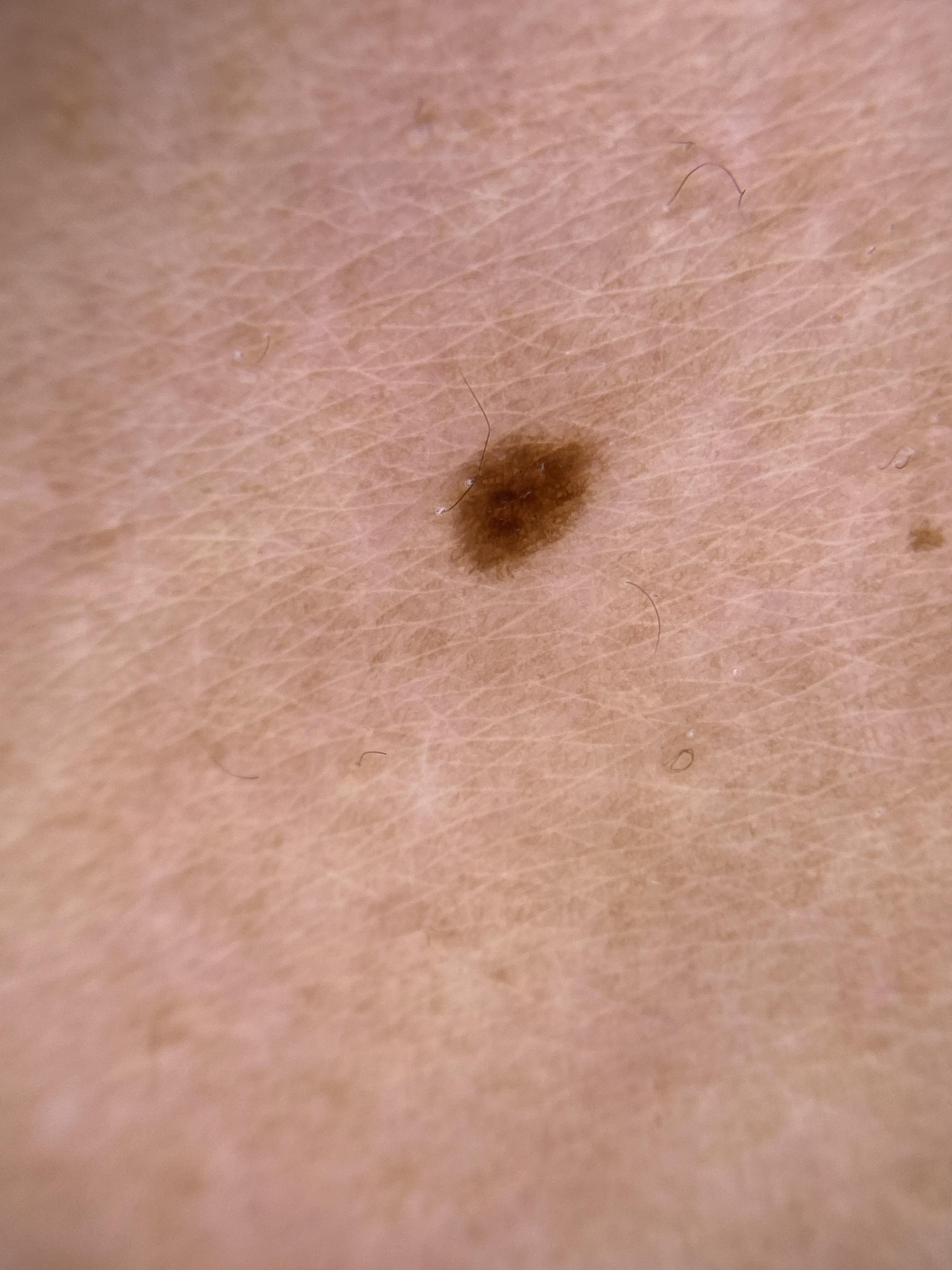A dermoscopic photograph of a skin lesion. A female patient aged 33 to 37. The lesion was found on the trunk. The diagnostic impression was a nevus.